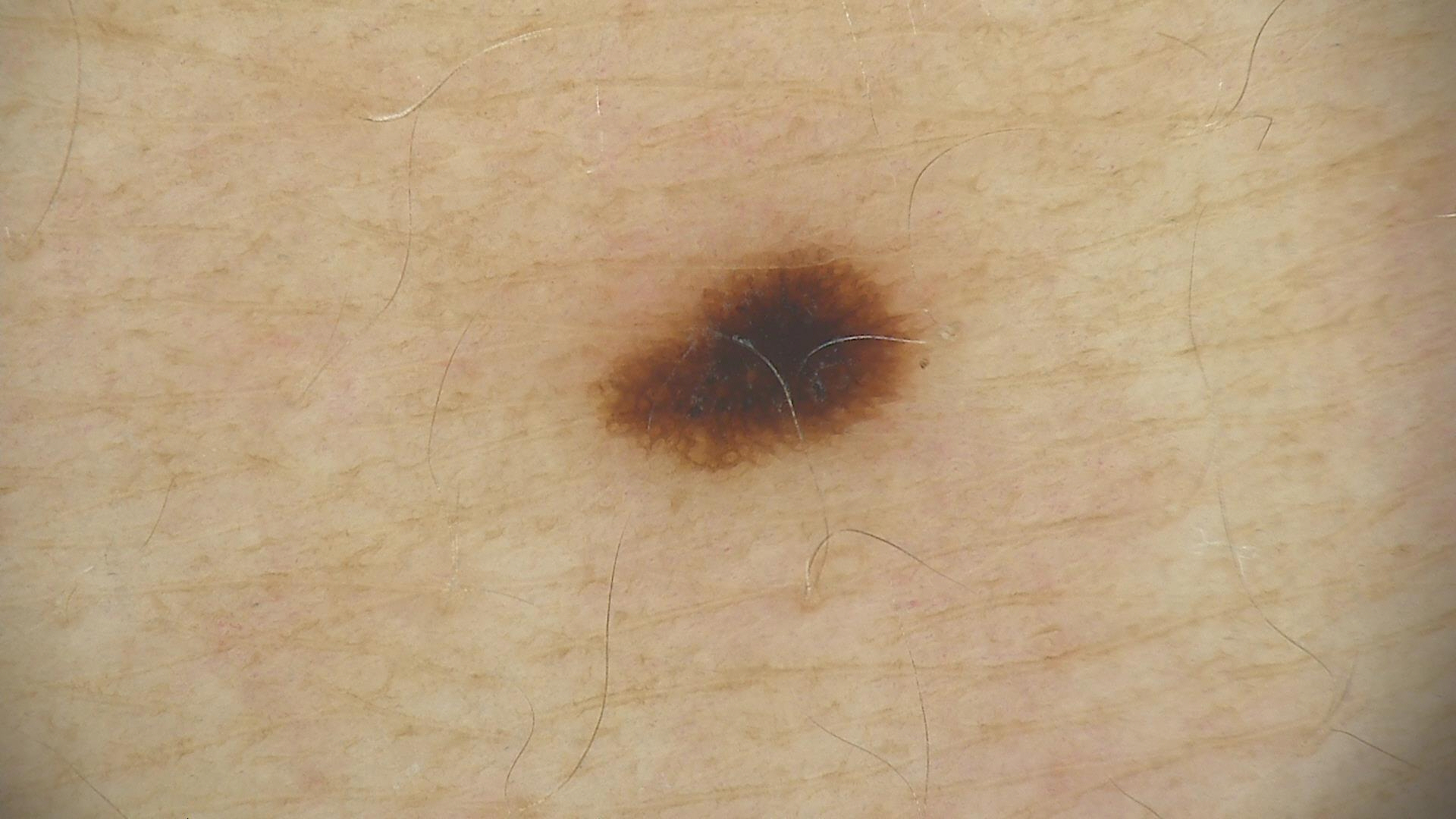Consistent with a dysplastic junctional nevus.